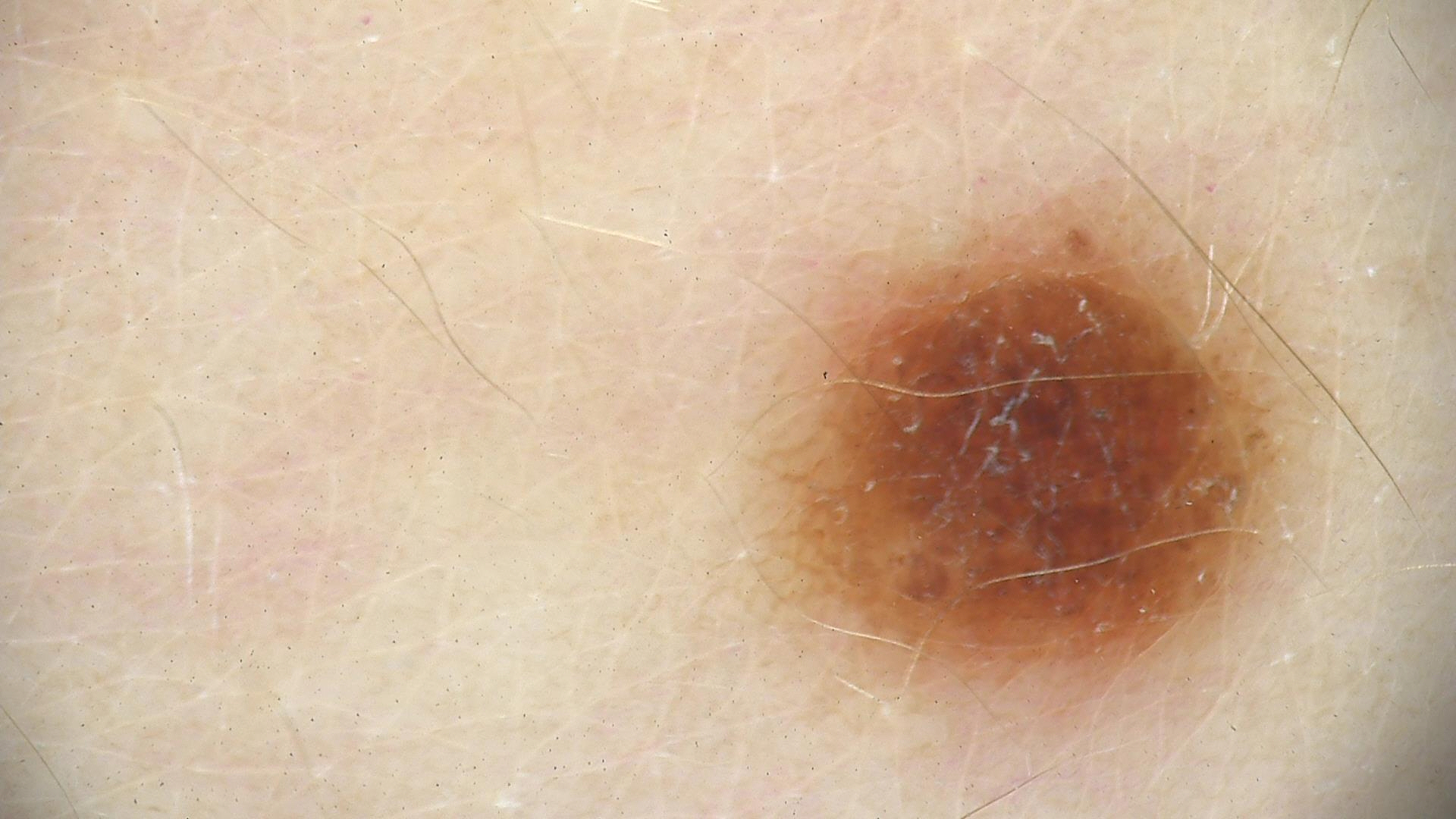imaging: dermoscopy | subtype: banal | class: compound nevus (expert consensus).